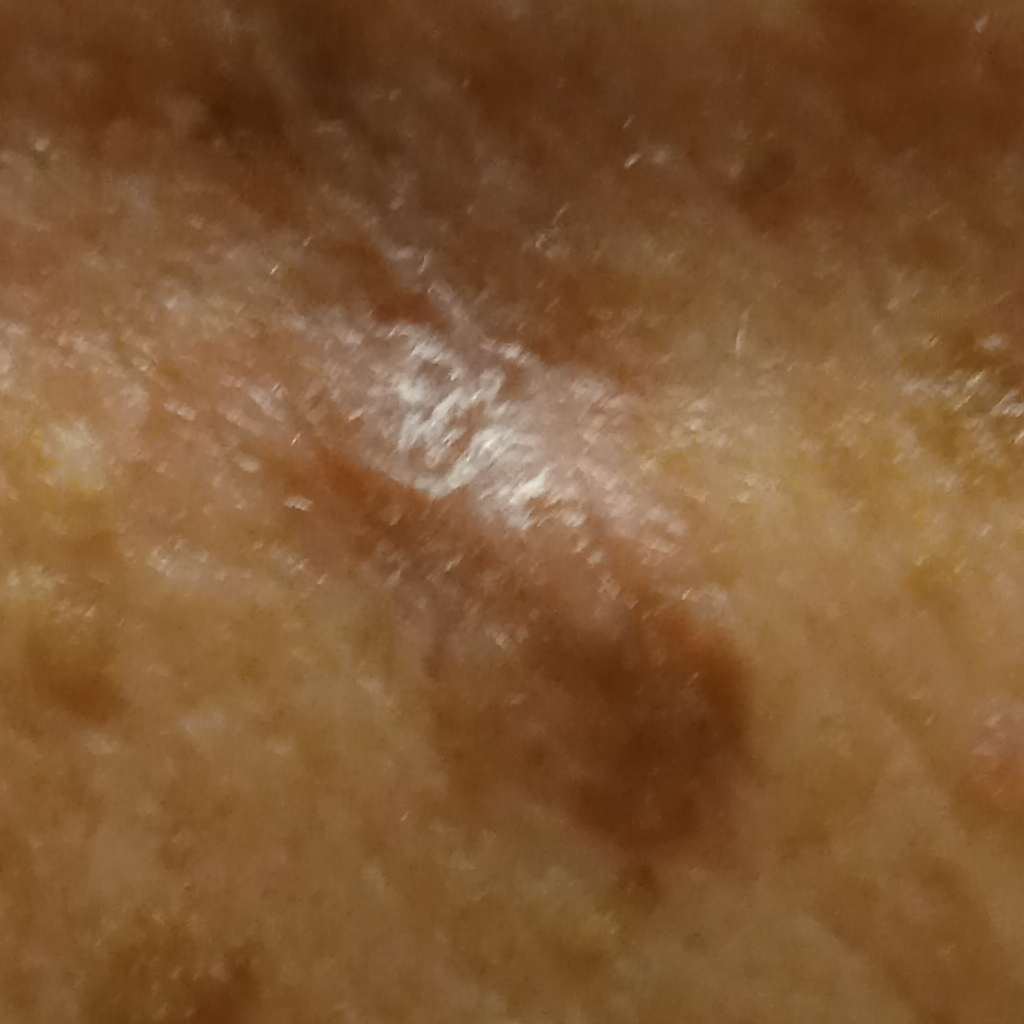By self-report, no personal history of cancer.
A clinical photograph of a skin lesion.
Few moles overall by the patient's own estimate.
A male patient age 62.
The patient says their skin reddens with sun exposure.
The lesion is about 13.8 mm across.
The lesion was assessed as a squamous cell carcinoma.